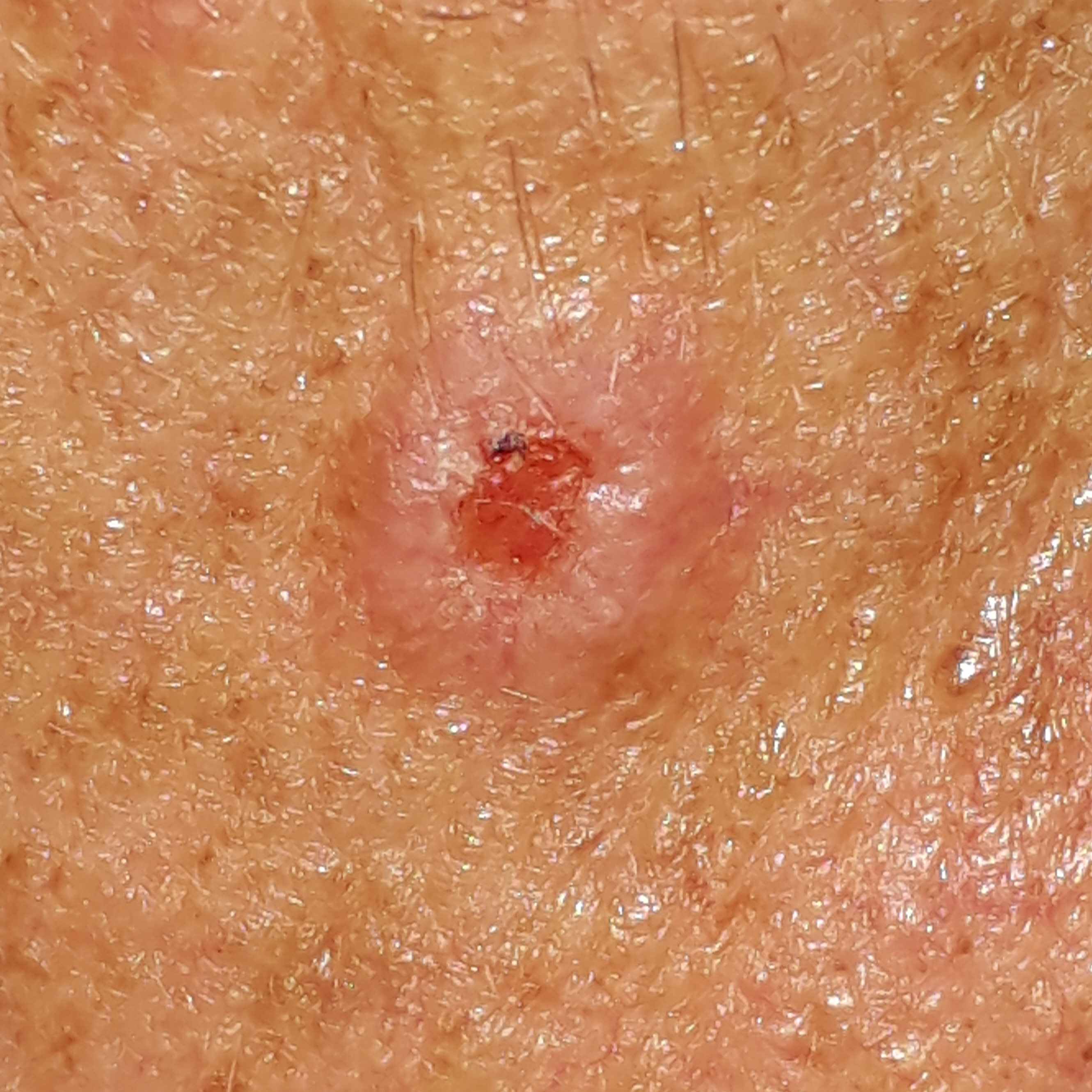The lesion involves the face.
Histopathologically confirmed as a basal cell carcinoma.